The leg and arm are involved · this is a close-up image · female contributor, age 30–39:
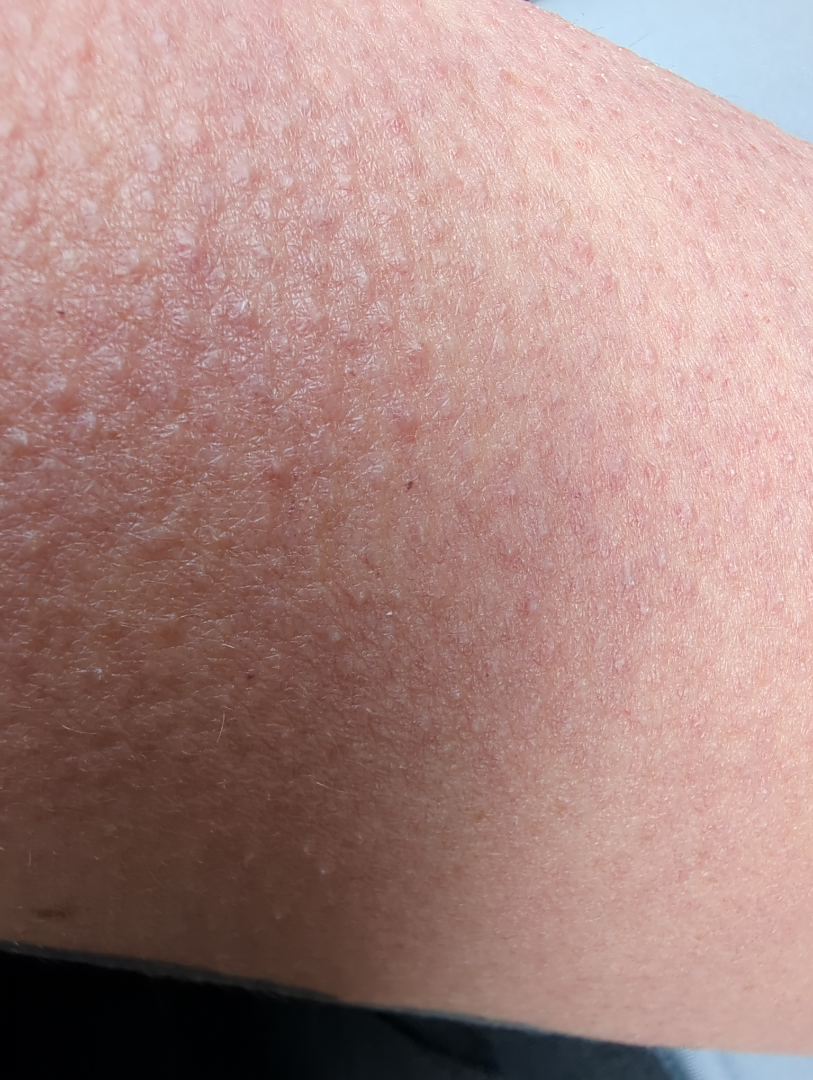Q: What was the assessment?
A: ungradable on photographic review